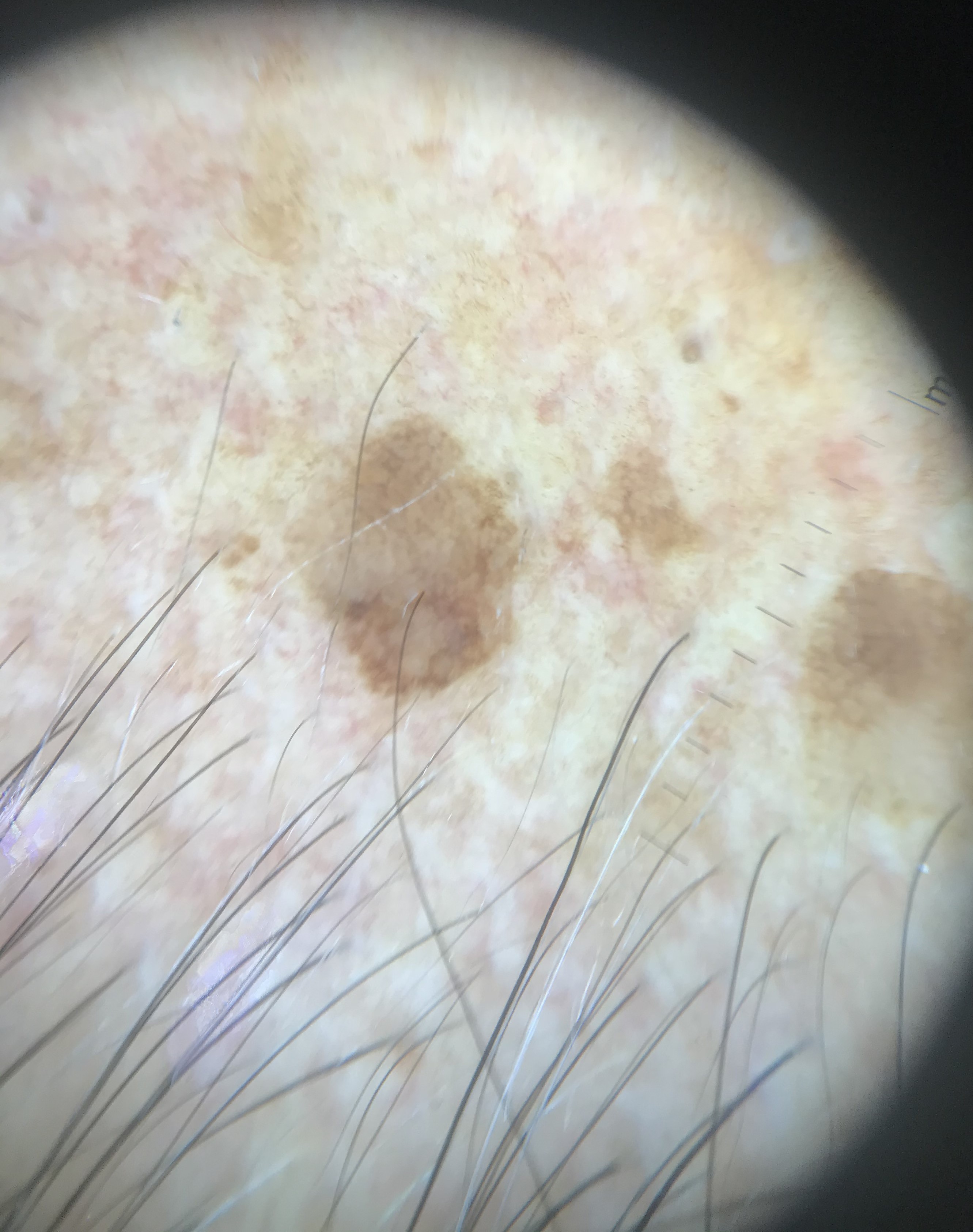This is a keratinocytic lesion. Consistent with a seborrheic keratosis.